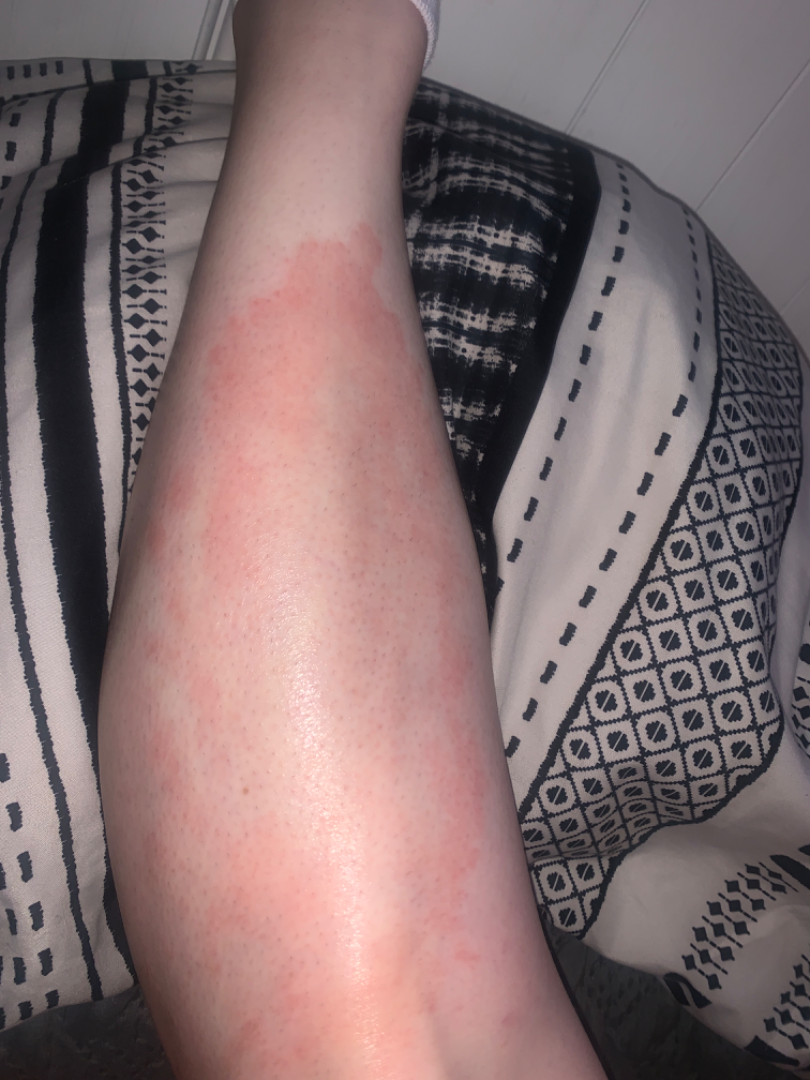Notes:
* shot type · close-up
* onset · more than one year
* body site · leg and arm
* skin tone · Fitzpatrick phototype III
* impression · Psoriasis (possible); Acute and chronic dermatitis (possible); Necrobiosis lipoidica (possible)